Symptoms reported: itching, burning and enlargement · the condition has been present for three to twelve months · female patient, age 40–49 · self-categorized by the patient as a rash · the lesion involves the leg and arm · close-up view · skin tone: Fitzpatrick skin type IV — 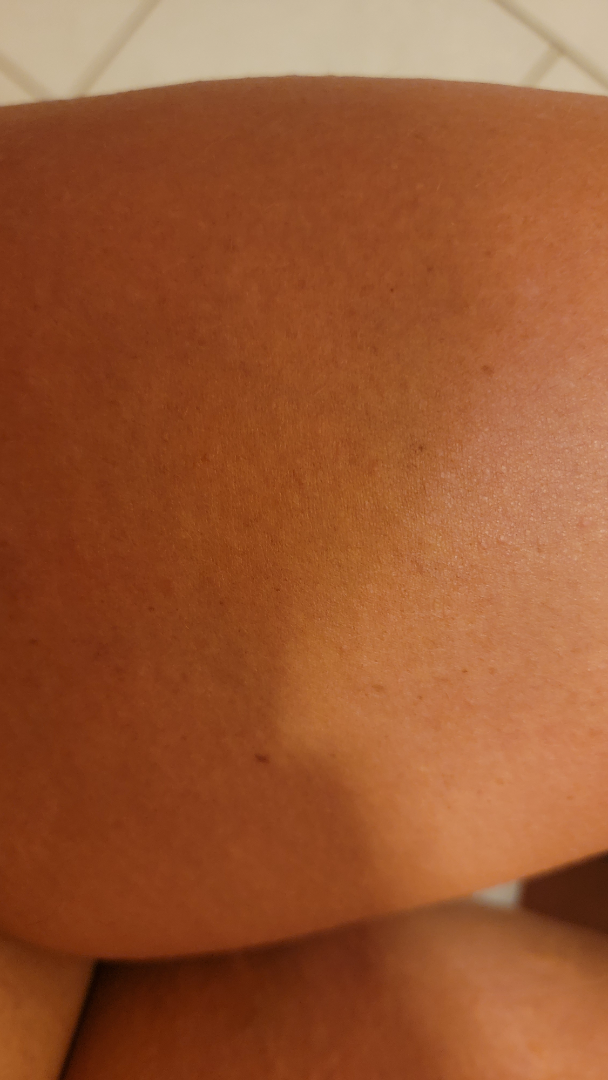<case>
  <assessment>none discernible</assessment>
</case>